Dermoscopy of a skin lesion: 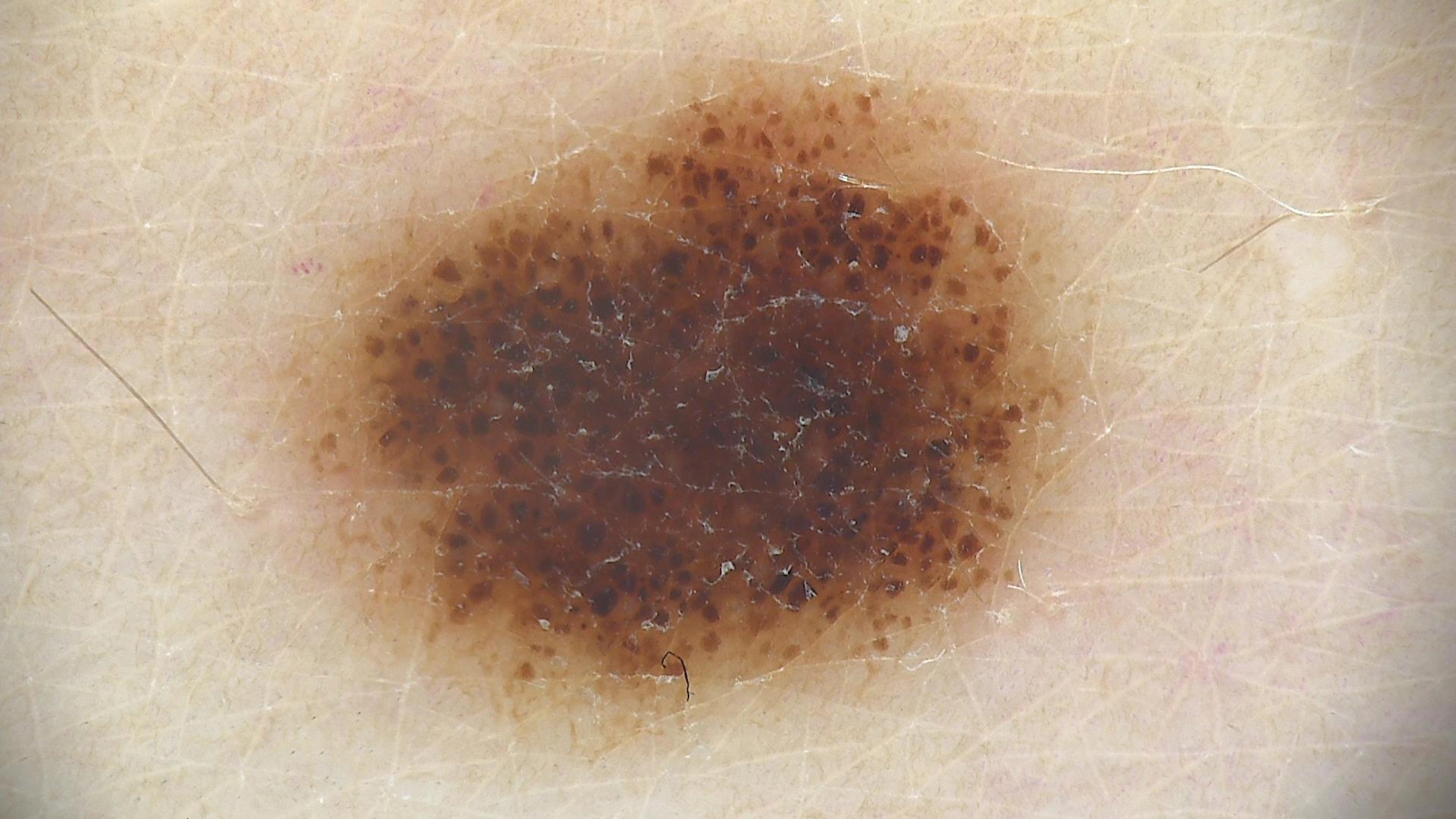| field | value |
|---|---|
| class | compound nevus (expert consensus) |